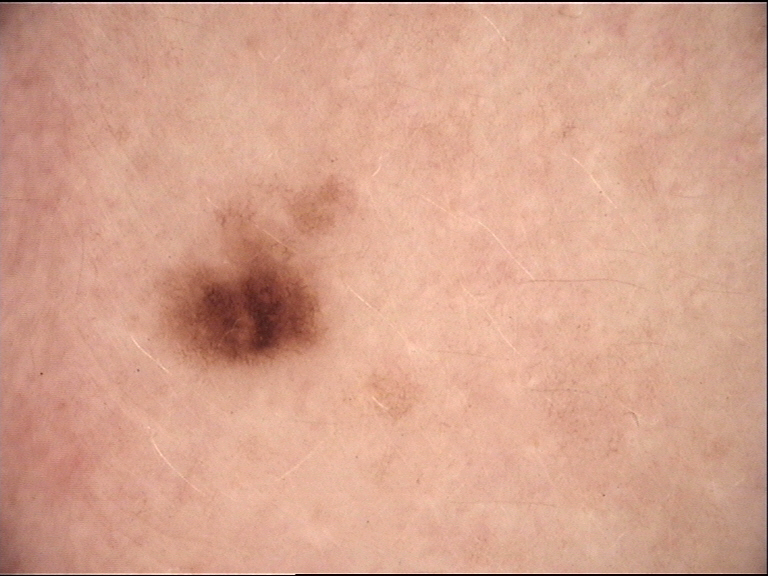Case:
• imaging — dermoscopy
• diagnosis — junctional nevus (expert consensus)